A macroscopic clinical photograph of a skin lesion. A male patient 62 years of age. Collected as part of a research study, without a referral diagnosis.
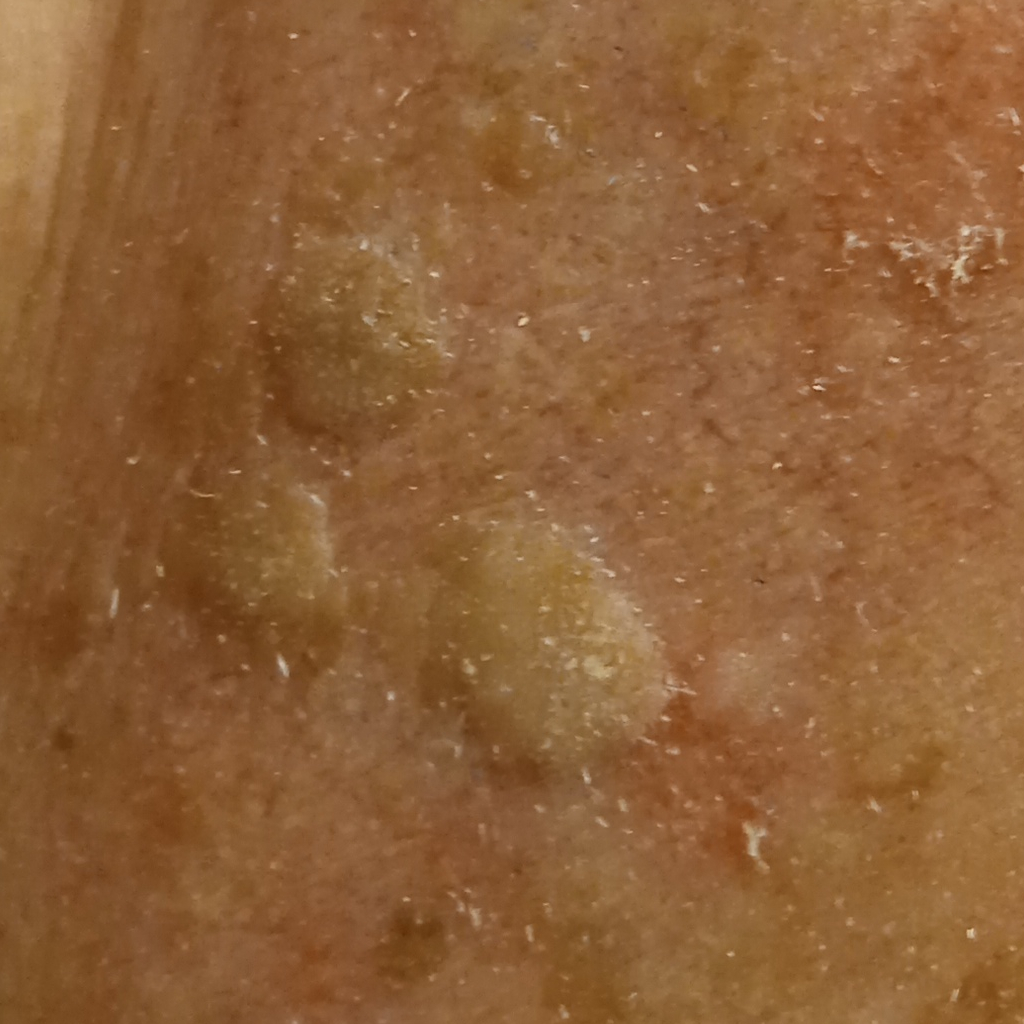| feature | finding |
|---|---|
| anatomic site | the face |
| size | 7.5 mm |
| diagnostic label | seborrheic keratosis (dermatologist consensus) |